A smartphone photograph of a skin lesion: 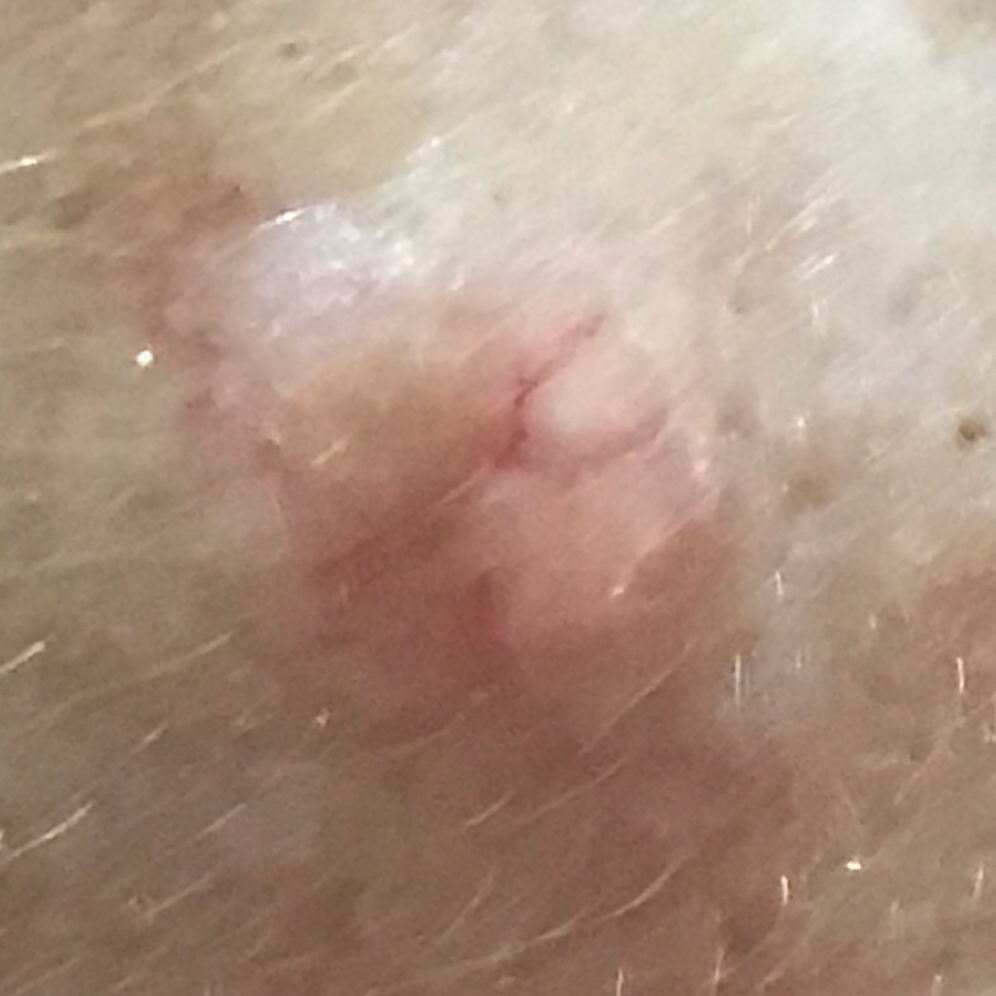* body site: the face
* lesion diameter: approx. 9 × 5 mm
* reported symptoms: elevation, growth / no change in appearance, no pain
* diagnosis: basal cell carcinoma (biopsy-proven)